Female patient, age 60–69. The lesion involves the back of the hand, leg and arm. The photo was captured at an angle: 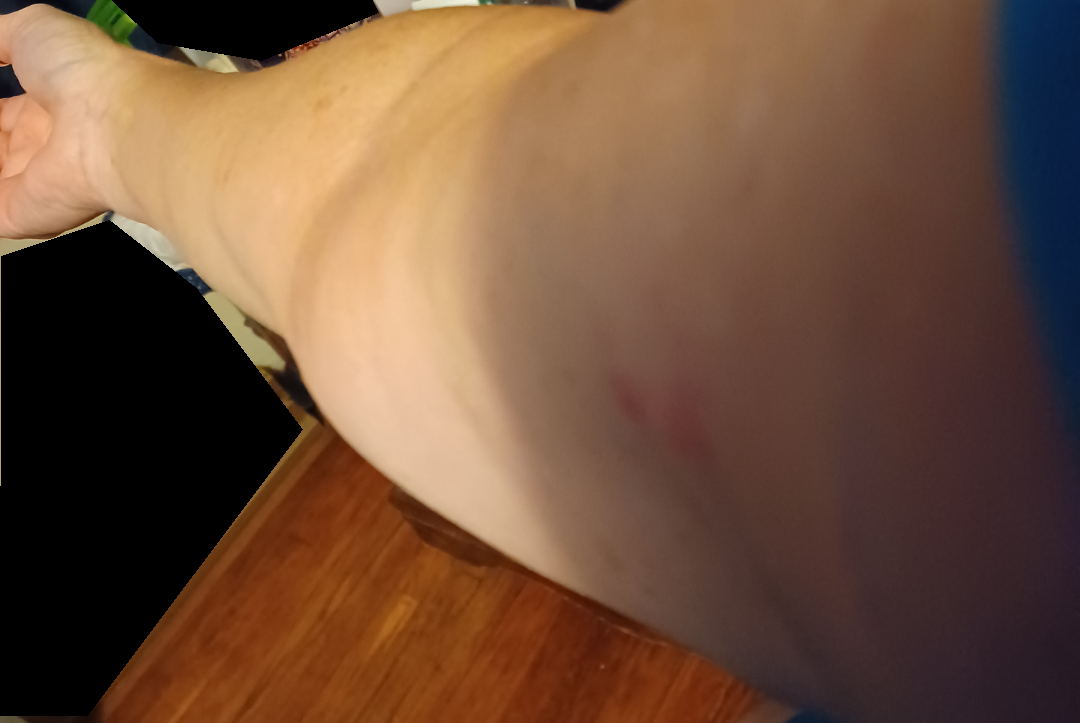assessment = not assessable; duration = about one day; reported symptoms = itching; described texture = raised or bumpy; constitutional symptoms = none reported.